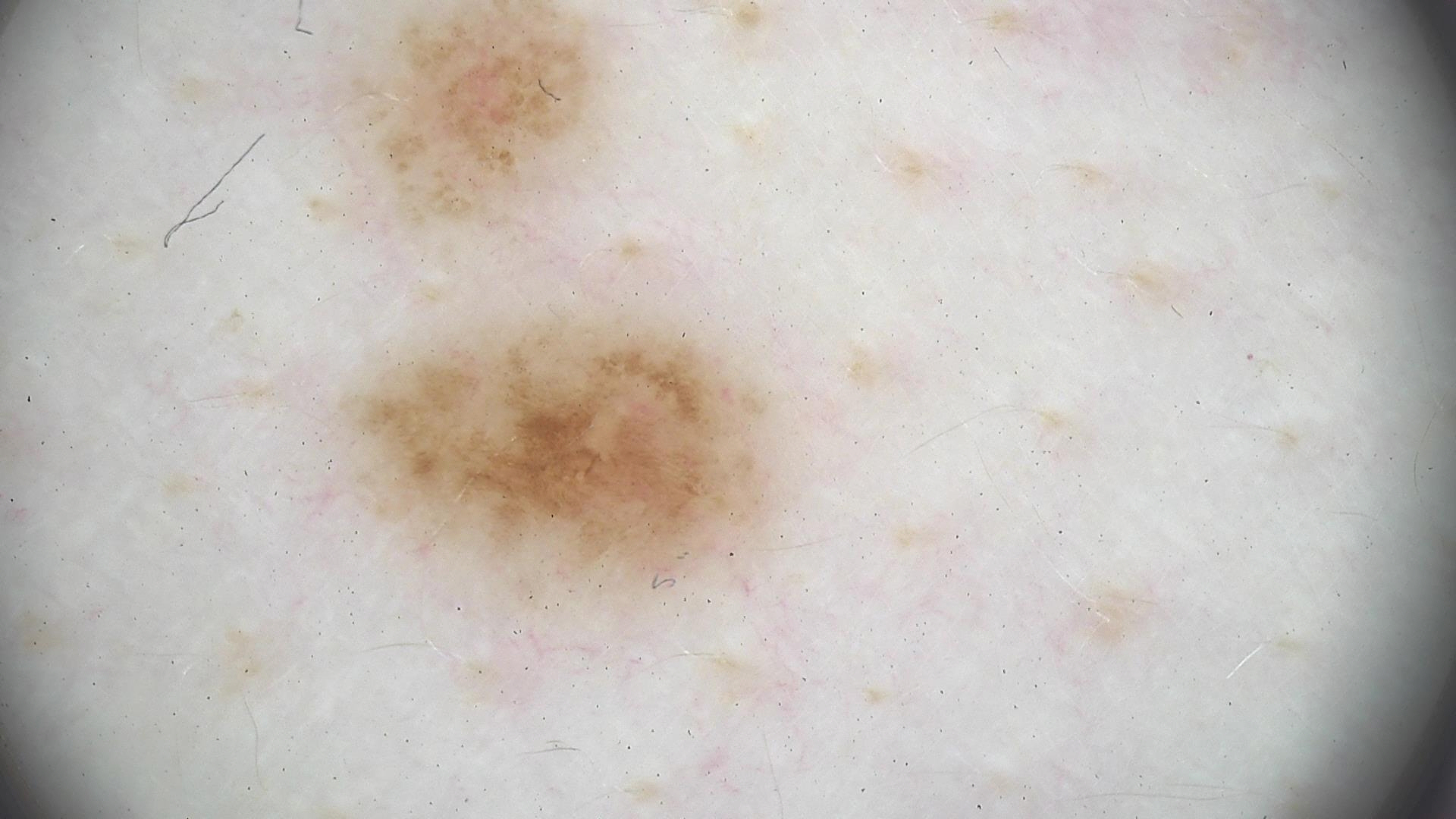Q: What kind of image is this?
A: dermatoscopy
Q: What was the diagnostic impression?
A: dysplastic junctional nevus (expert consensus)